A patient 45 years of age. A smartphone photograph of a skin lesion: 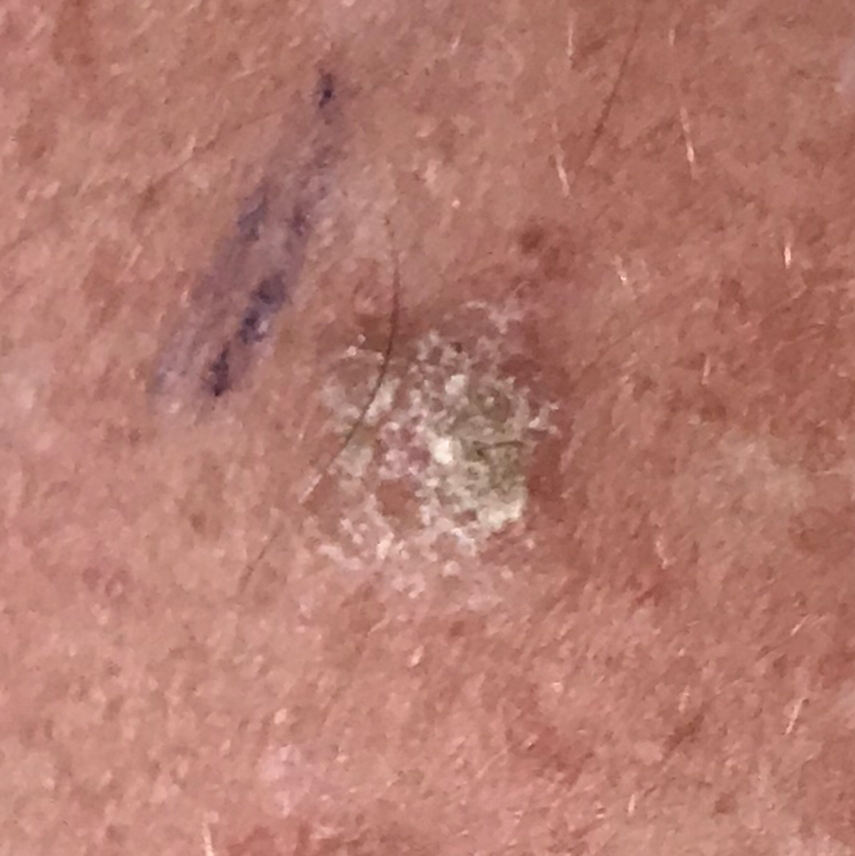<skin_lesion>
  <lesion_location>an arm</lesion_location>
  <symptoms>
    <present>itching, growth</present>
  </symptoms>
  <diagnosis>
    <name>actinic keratosis</name>
    <code>ACK</code>
    <malignancy>indeterminate</malignancy>
    <confirmation>clinical consensus</confirmation>
  </diagnosis>
</skin_lesion>